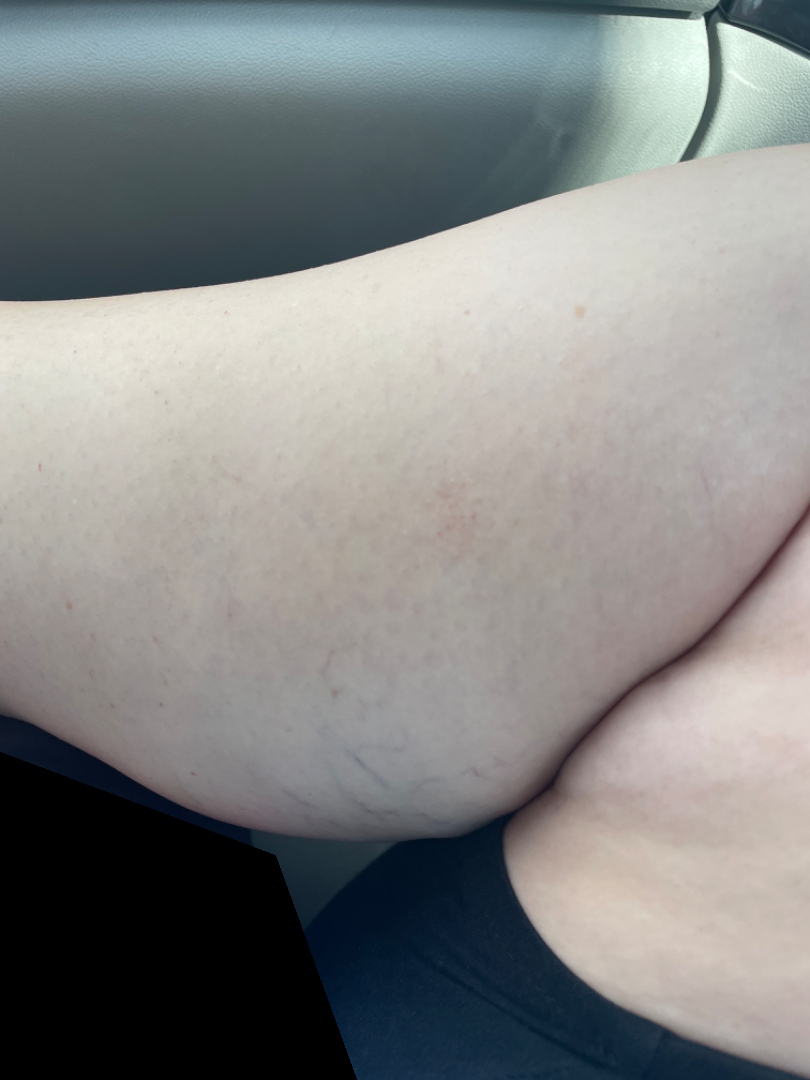image framing — at a distance | dermatologist impression — Lichen spinulosus (0.67); Eczema (0.33).